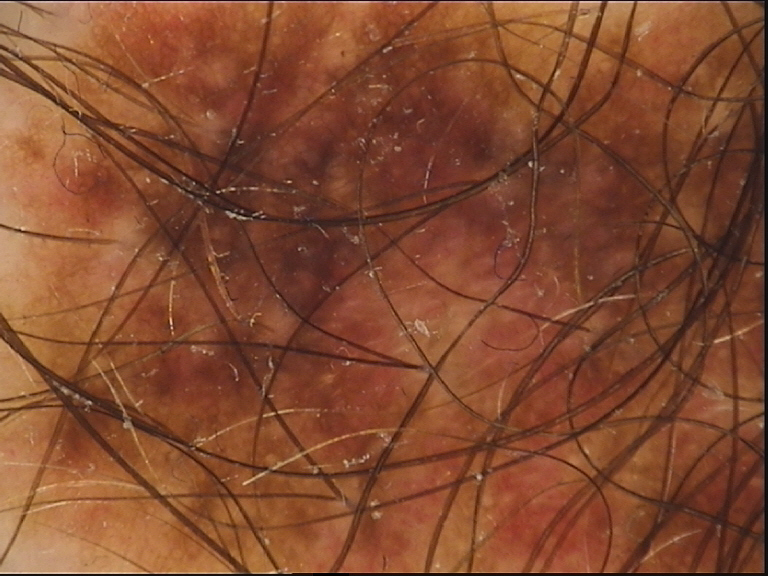| feature | finding |
|---|---|
| image type | dermoscopy |
| assessment | compound nevus (expert consensus) |